A dermatoscopic image of a skin lesion.
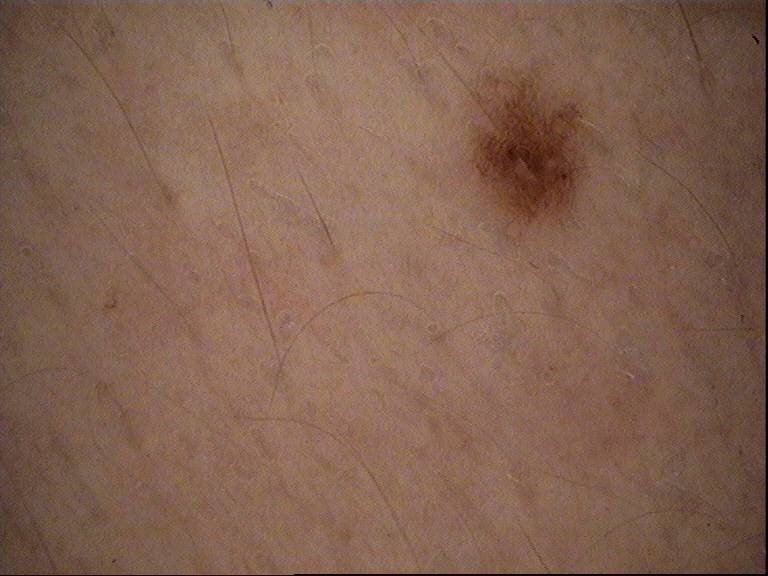<case>
  <diagnosis>
    <name>dysplastic junctional nevus</name>
    <code>jd</code>
    <malignancy>benign</malignancy>
    <super_class>melanocytic</super_class>
    <confirmation>expert consensus</confirmation>
  </diagnosis>
</case>